Female patient, age 30–39. Close-up view. The patient indicates the condition has been present for less than one week. The lesion involves the leg, arm, head or neck, back of the hand, back of the torso and front of the torso. No relevant systemic symptoms. The lesion is described as raised or bumpy. Symptoms reported: itching, burning and pain: 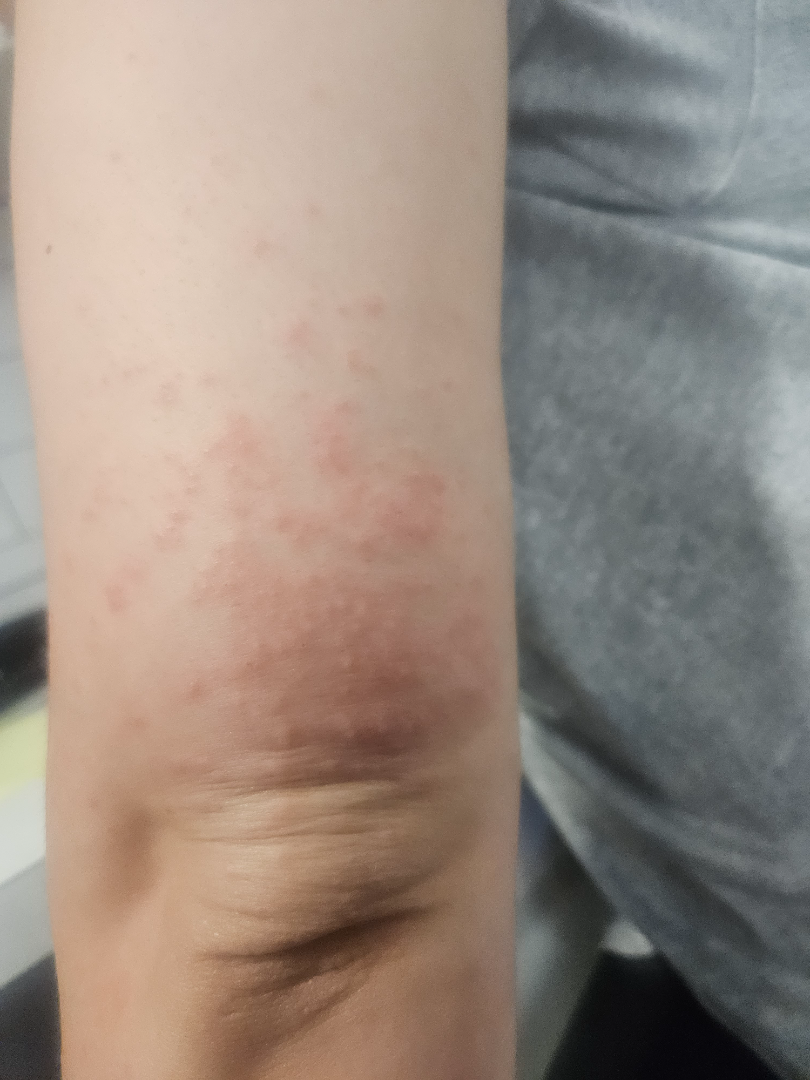The case was difficult to assess from the available photograph.